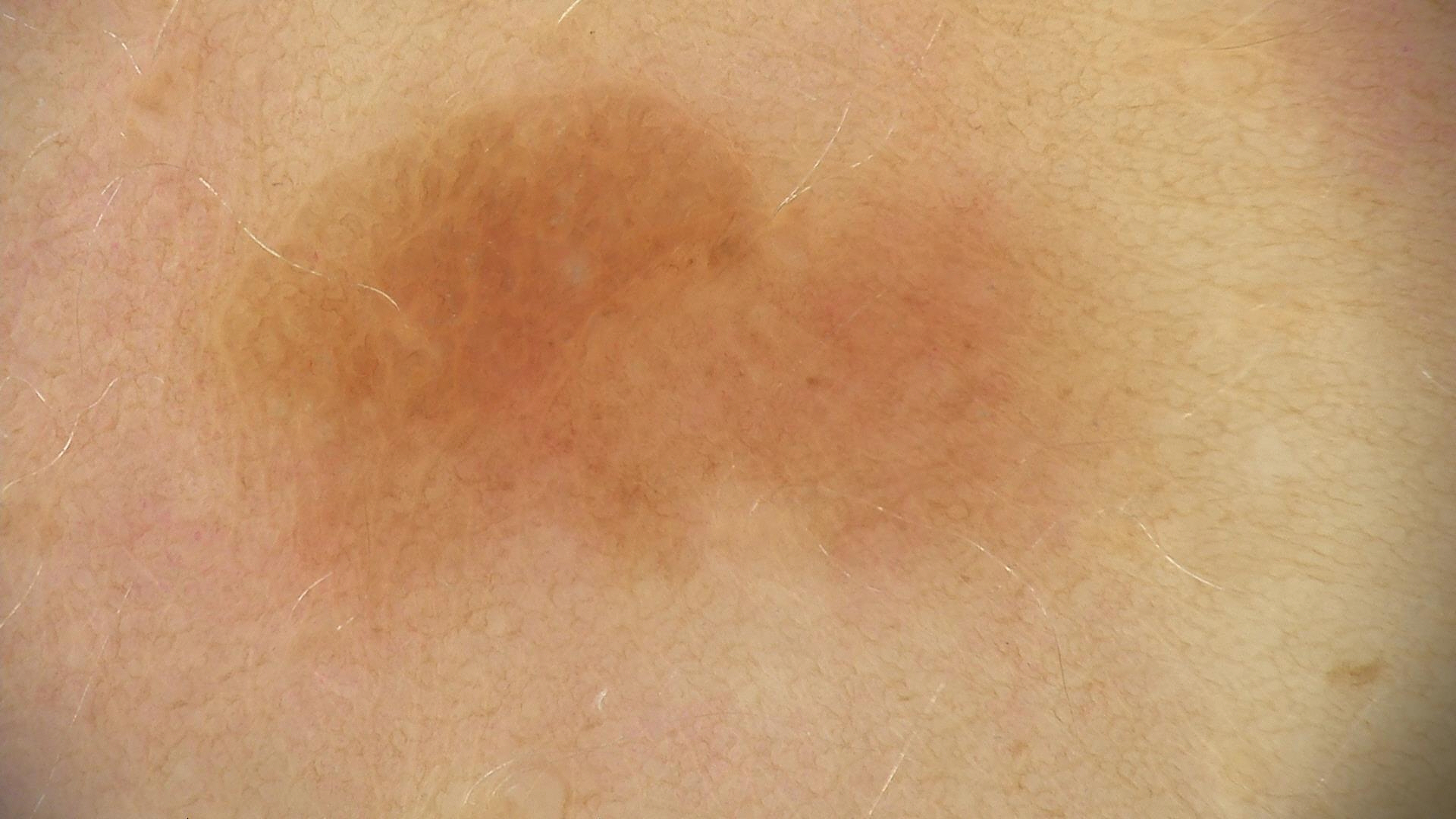{"image": "dermoscopy", "lesion_type": {"main_class": "keratinocytic"}, "diagnosis": {"name": "seborrheic keratosis", "code": "sk", "malignancy": "benign", "super_class": "non-melanocytic", "confirmation": "expert consensus"}}